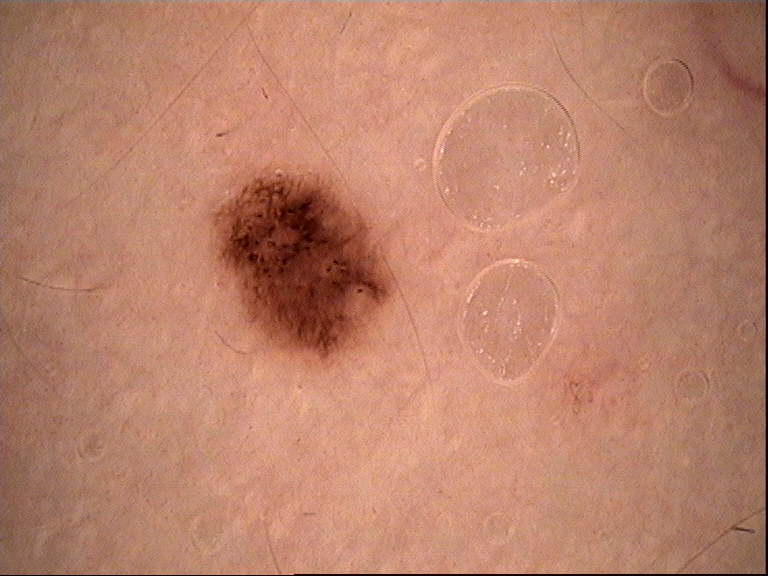Consistent with a dysplastic junctional nevus.